A dermoscopy image of a single skin lesion.
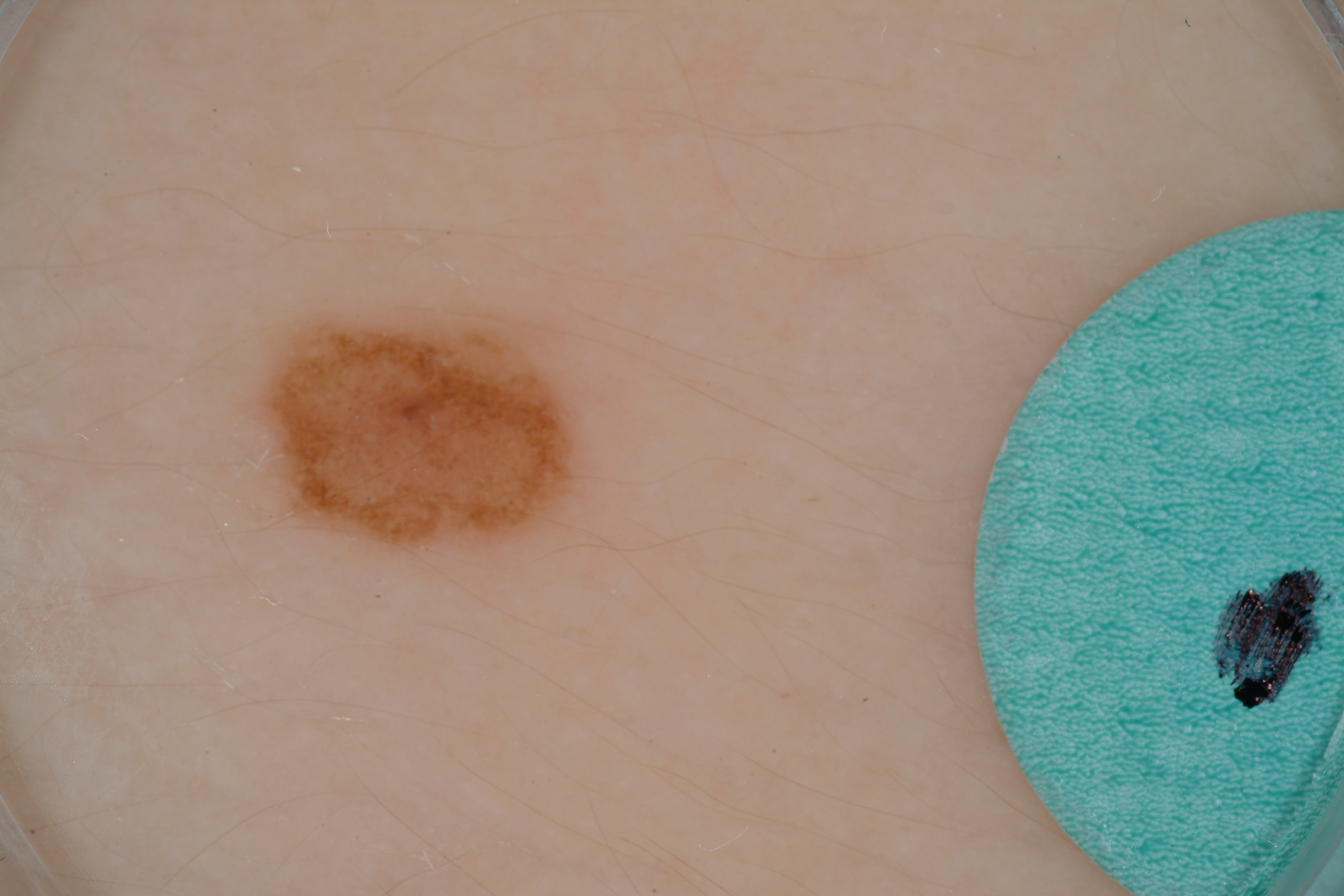Dermoscopy demonstrates no streaks, milia-like cysts, pigment network, or negative network. As (left, top, right, bottom), the visible lesion spans bbox=[245, 305, 586, 559]. Clinically diagnosed as a melanocytic nevus, a benign lesion.